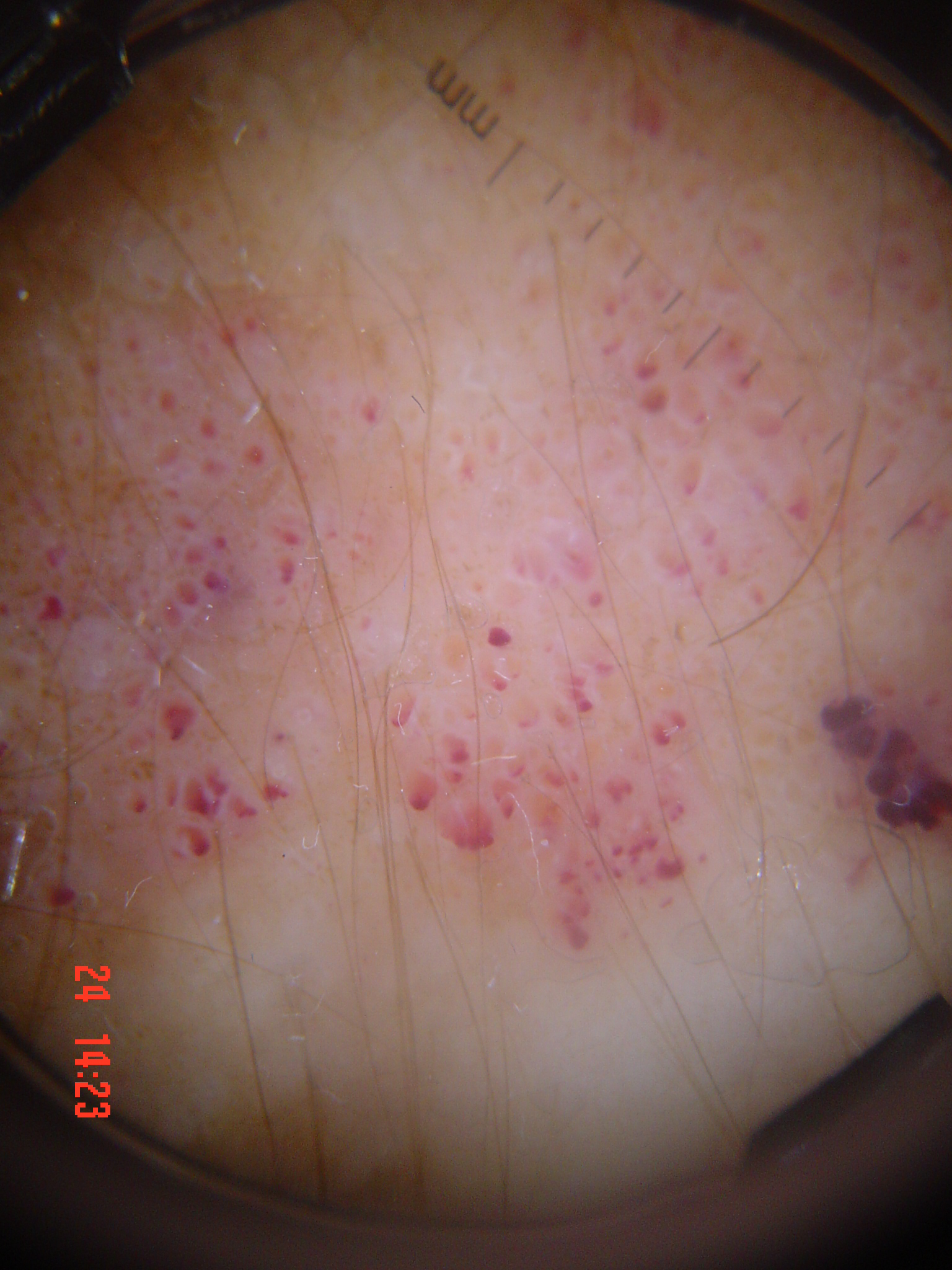Case:
A dermoscopic image of a skin lesion. The architecture is that of a vascular lesion.
Impression:
Classified as a lymphangioma.